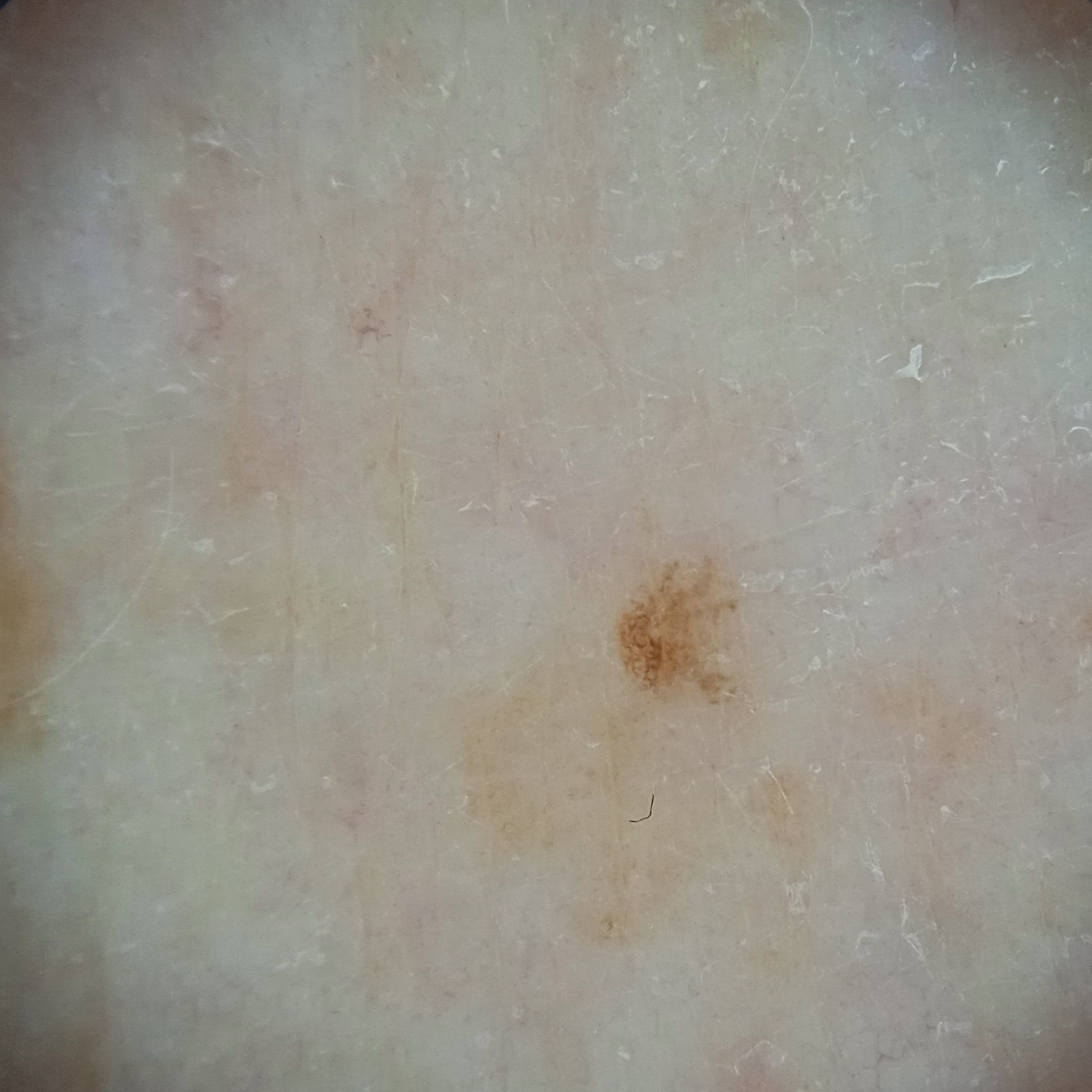Collected as part of a research study, without a referral diagnosis. The patient says their skin reddens with sun exposure. A dermoscopy image of a skin lesion. The patient reports a personal history of cancer and a personal history of skin cancer. A female patient 71 years old. Few moles overall by the patient's own estimate. The lesion involves an arm. Measuring roughly 1.7 mm. The four-dermatologist consensus diagnosis was a melanocytic nevus; the reviewers' opinions were divided; diagnostic confidence was good.